This image was taken at a distance; the affected area is the leg.
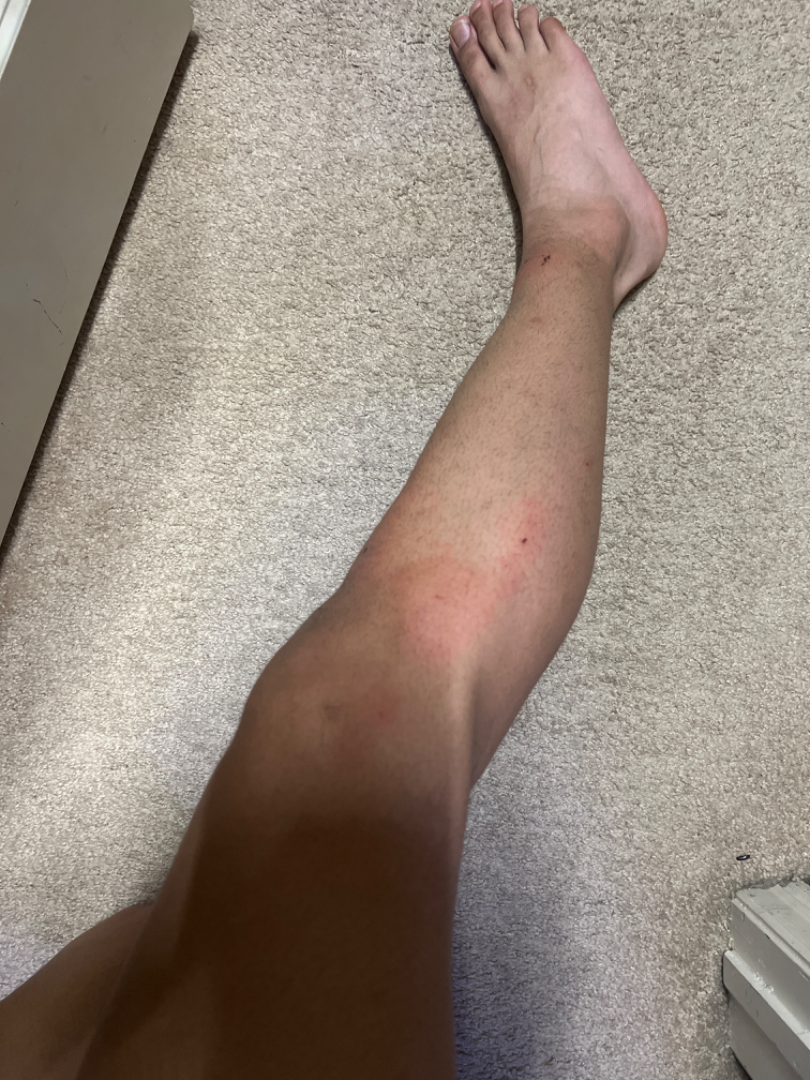The lesion is described as raised or bumpy.
The patient described the issue as a rash.
The contributor notes the condition has been present for less than one week.
No constitutional symptoms were reported.
On teledermatology review: Urticaria (67%); Allergic Contact Dermatitis (33%).